A dermoscopy image of a single skin lesion.
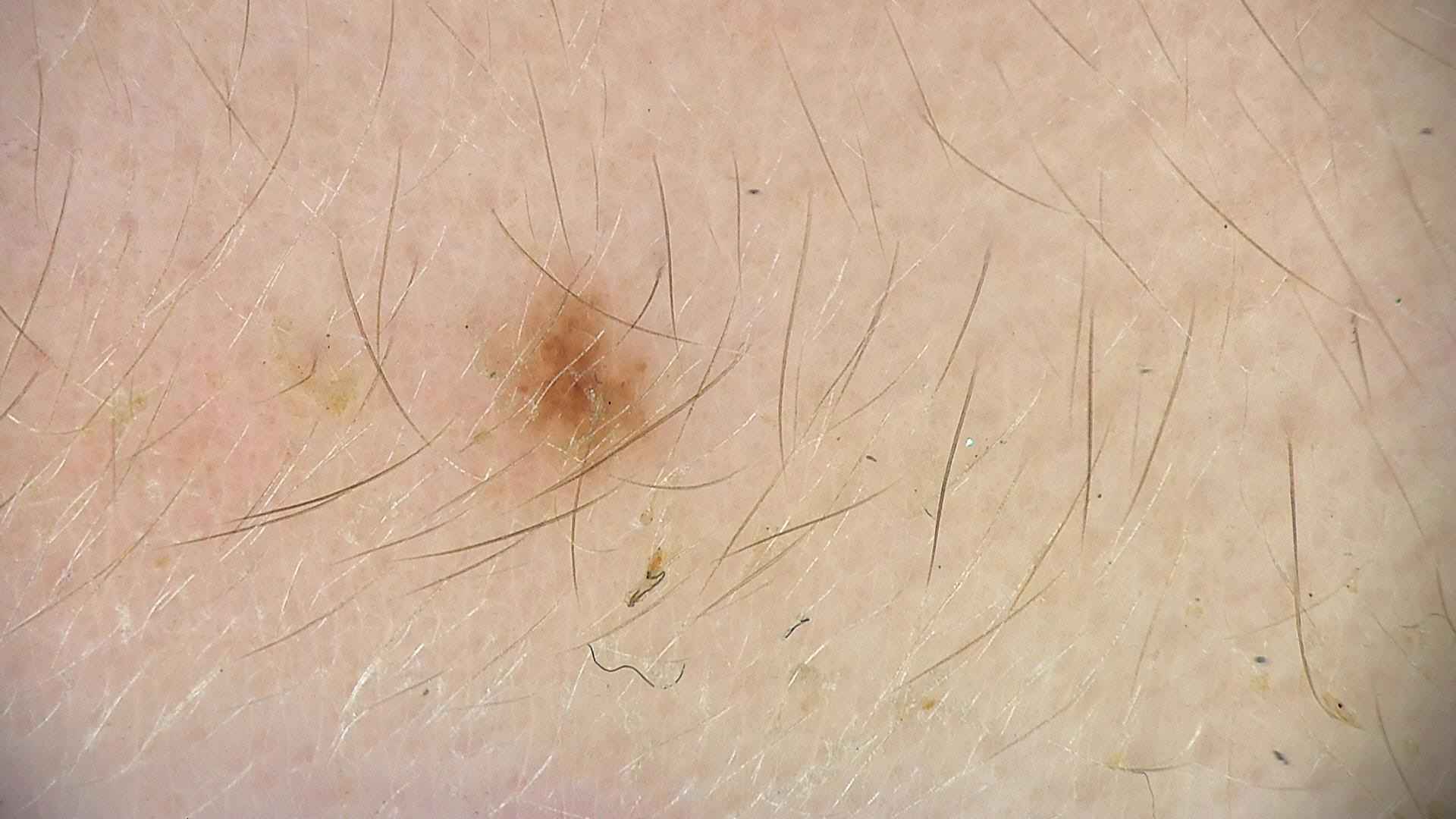assessment: dysplastic junctional nevus (expert consensus).